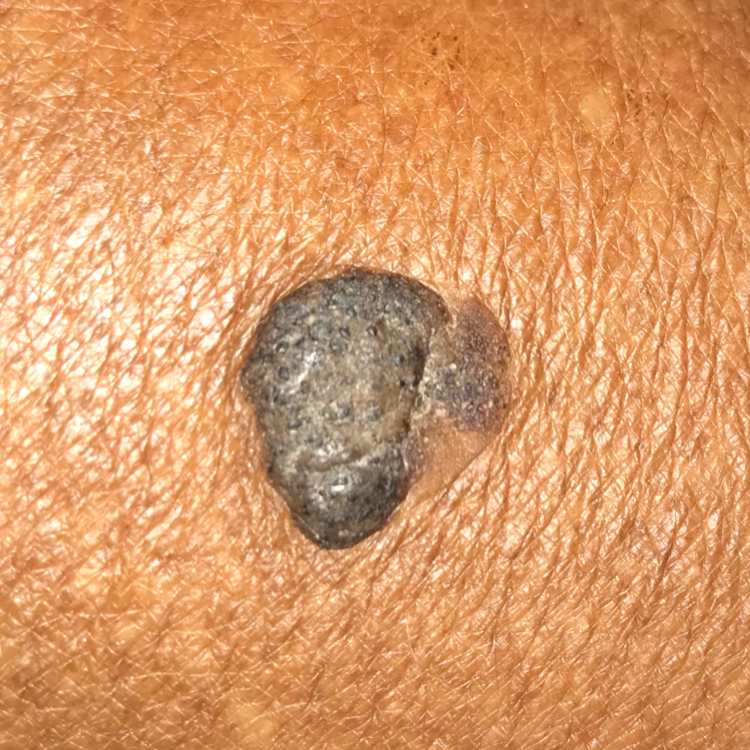A subject in their 70s.
By the patient's account, the lesion is elevated and has grown.
The clinical impression was a benign lesion — a seborrheic keratosis.